The lesion is described as rough or flaky and flat; female patient, age 50–59; the patient did not report lesion symptoms; present for one to four weeks; the photo was captured at a distance; the lesion involves the leg:
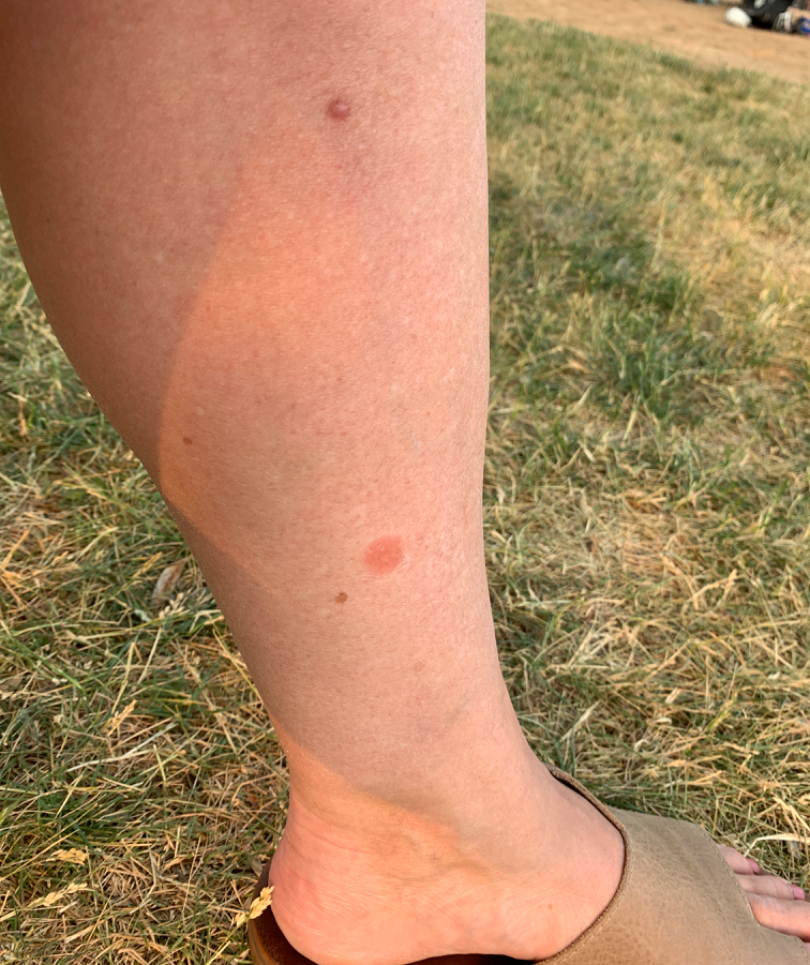The dermatologist could not determine a likely condition from the photograph alone.